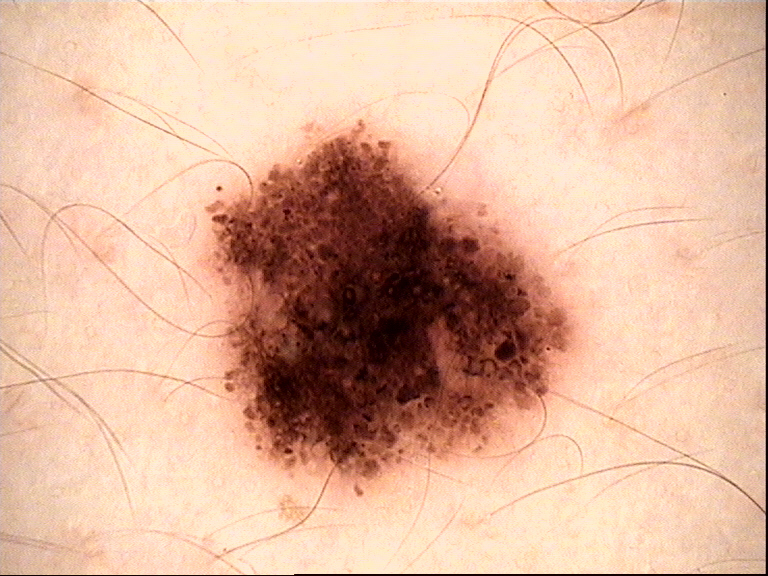<lesion>
  <image>dermatoscopy</image>
  <diagnosis>
    <name>dysplastic compound nevus</name>
    <code>cd</code>
    <malignancy>benign</malignancy>
    <super_class>melanocytic</super_class>
    <confirmation>expert consensus</confirmation>
  </diagnosis>
</lesion>